A female subject in their mid- to late 20s · the patient is Fitzpatrick skin type I — 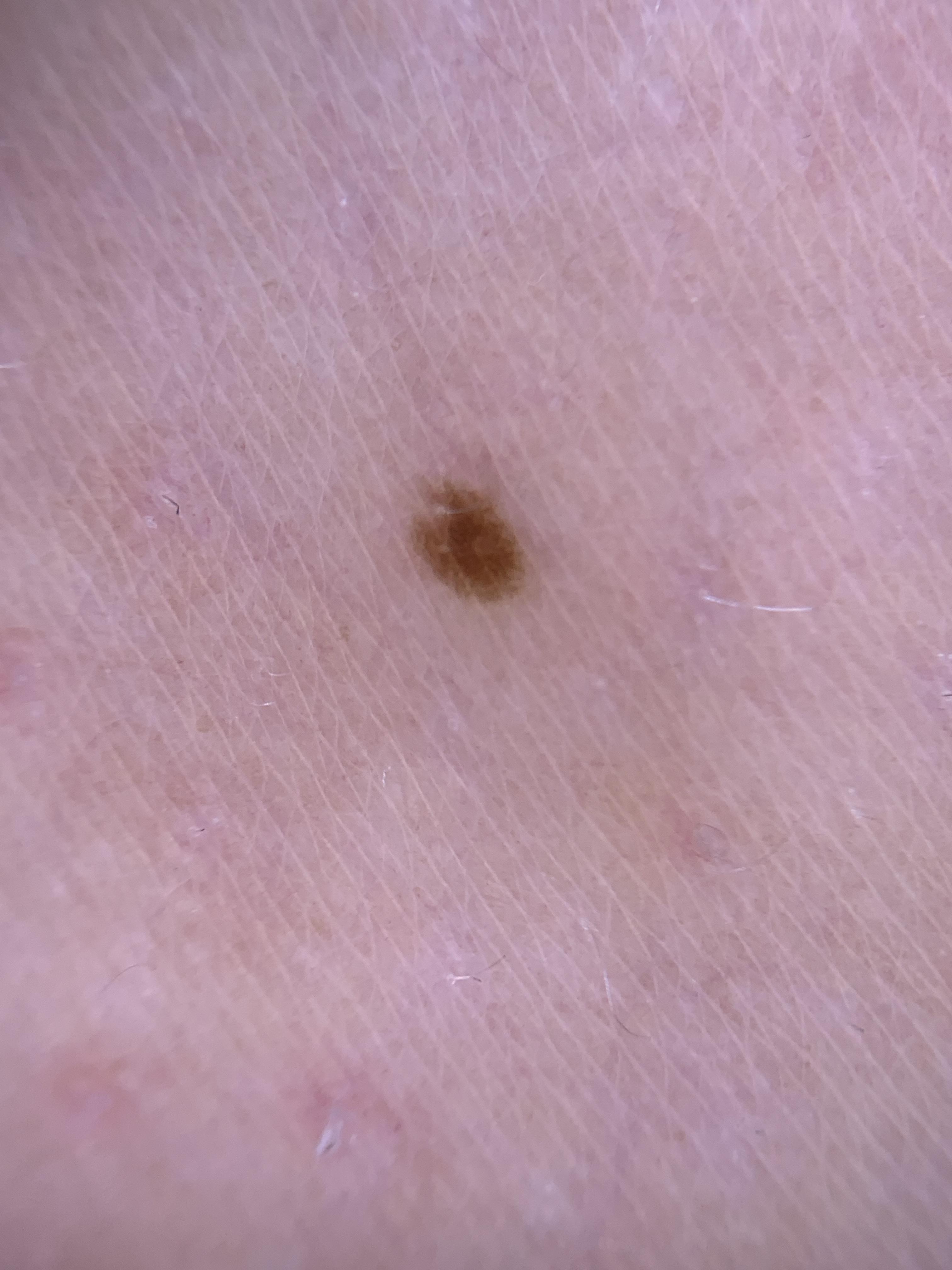The lesion is on an upper extremity. The clinical impression was a benign, melanocytic lesion — a nevus.